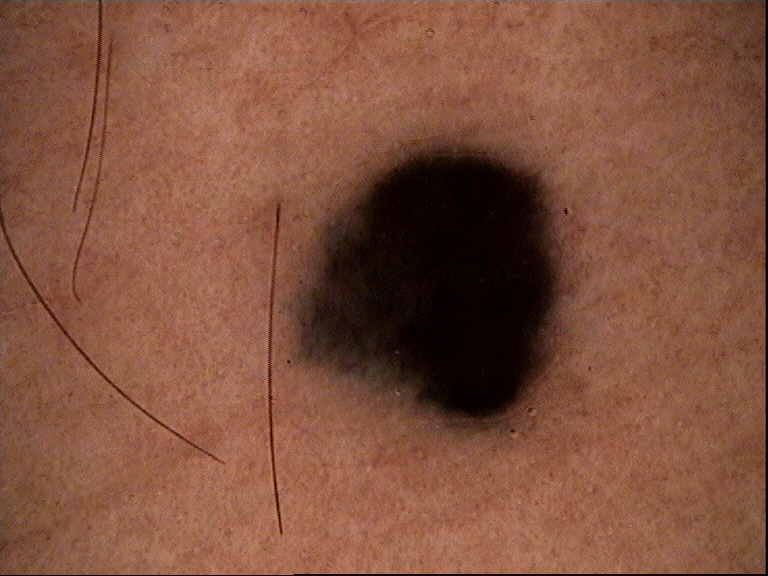Case:
* lesion type · banal, dermal
* label · blue nevus (expert consensus)